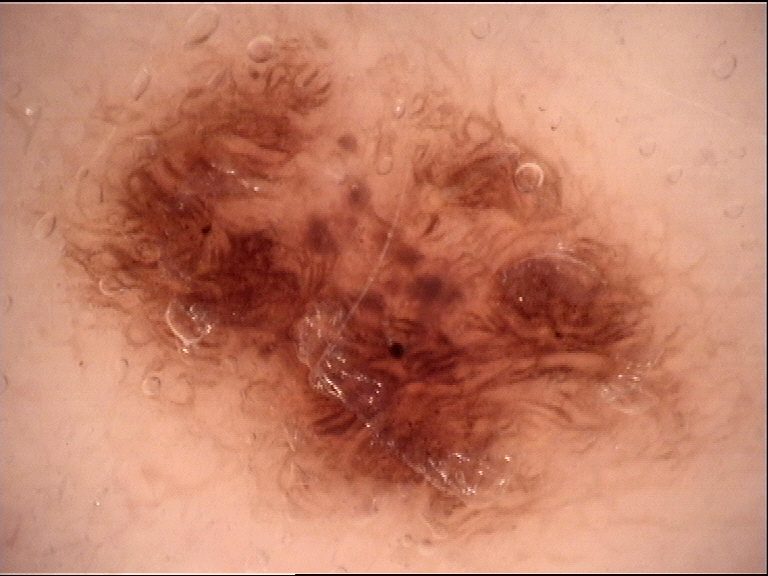image type: dermoscopy; diagnostic label: dysplastic junctional nevus (expert consensus).